A dermoscopic image of a skin lesion.
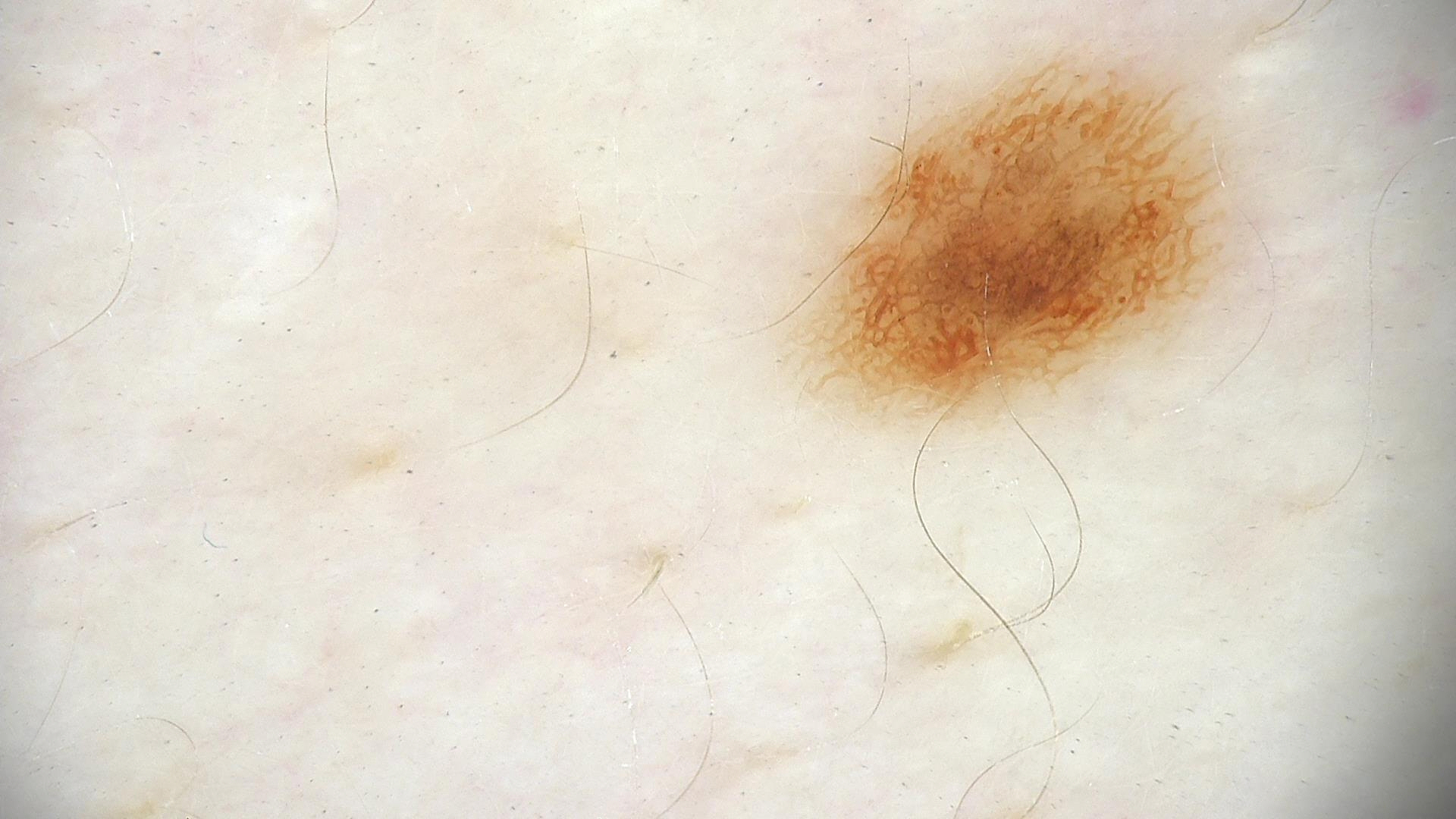The diagnostic label was a dysplastic junctional nevus.